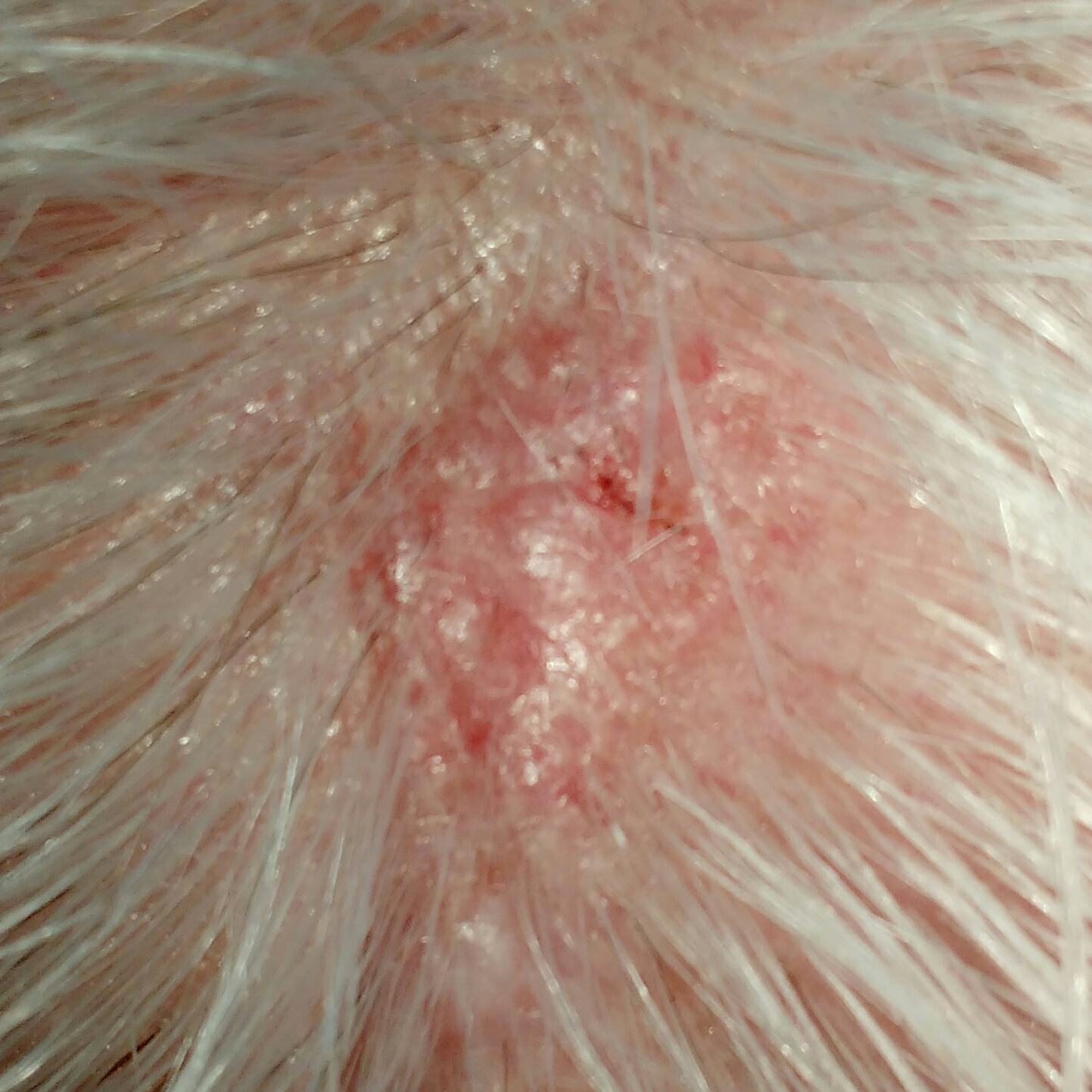FST = II
image type = clinical photo
subject = female, in their 70s
region = the face
lesion size = 20 × 16 mm
symptoms = bleeding, elevation, itching
diagnostic label = basal cell carcinoma (biopsy-proven)